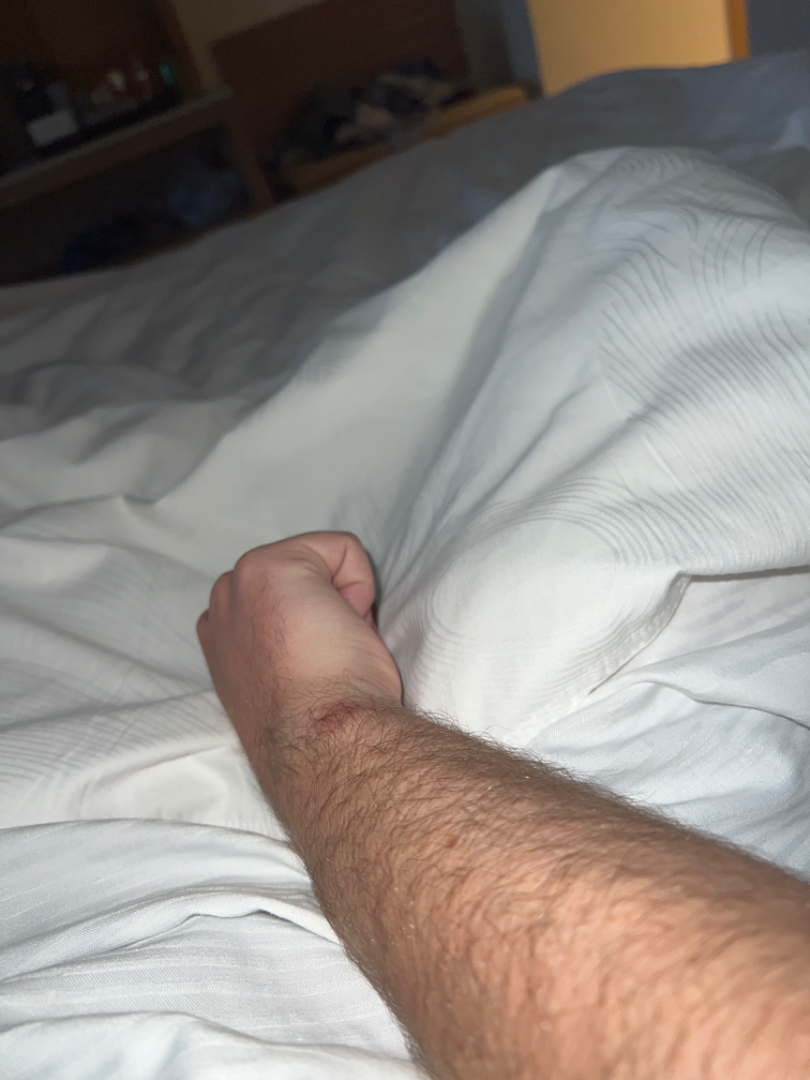Case summary:
* assessment — not assessable